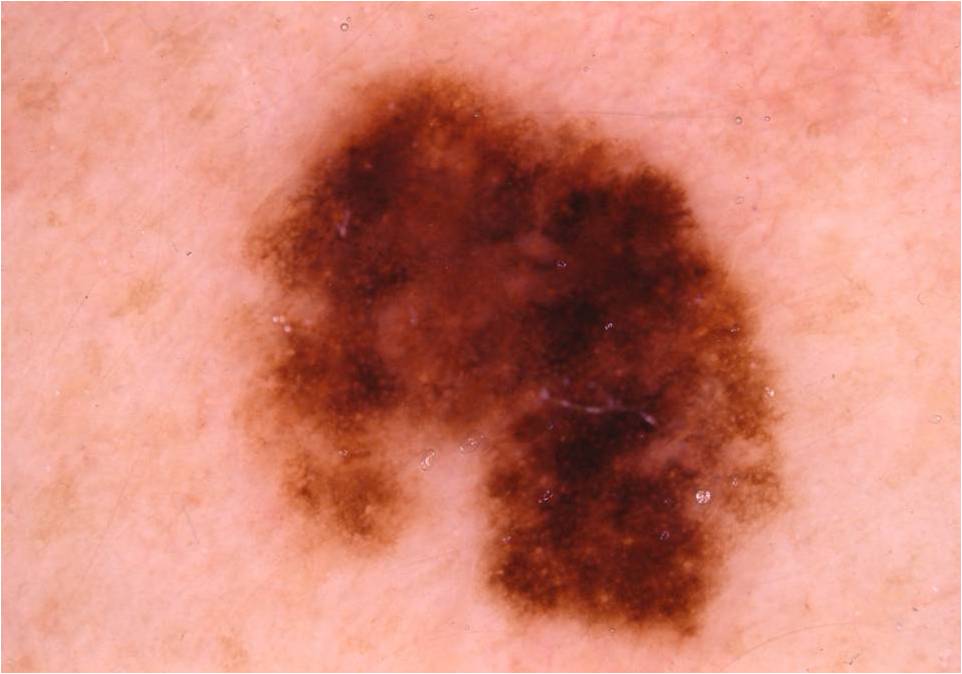subject = female, in their mid-30s
image = dermoscopic image
lesion location = <bbox>237, 63, 783, 645</bbox>
dermoscopic features = pigment network and streaks; absent: milia-like cysts, negative network, and globules
impression = a melanoma